The patient says their skin reddens painfully with sun exposure · a female patient 55 years old · by self-report, immunosuppression and a prior organ transplant · a moderate number of moles by the patient's own estimate · a dermoscopy image of a skin lesion — 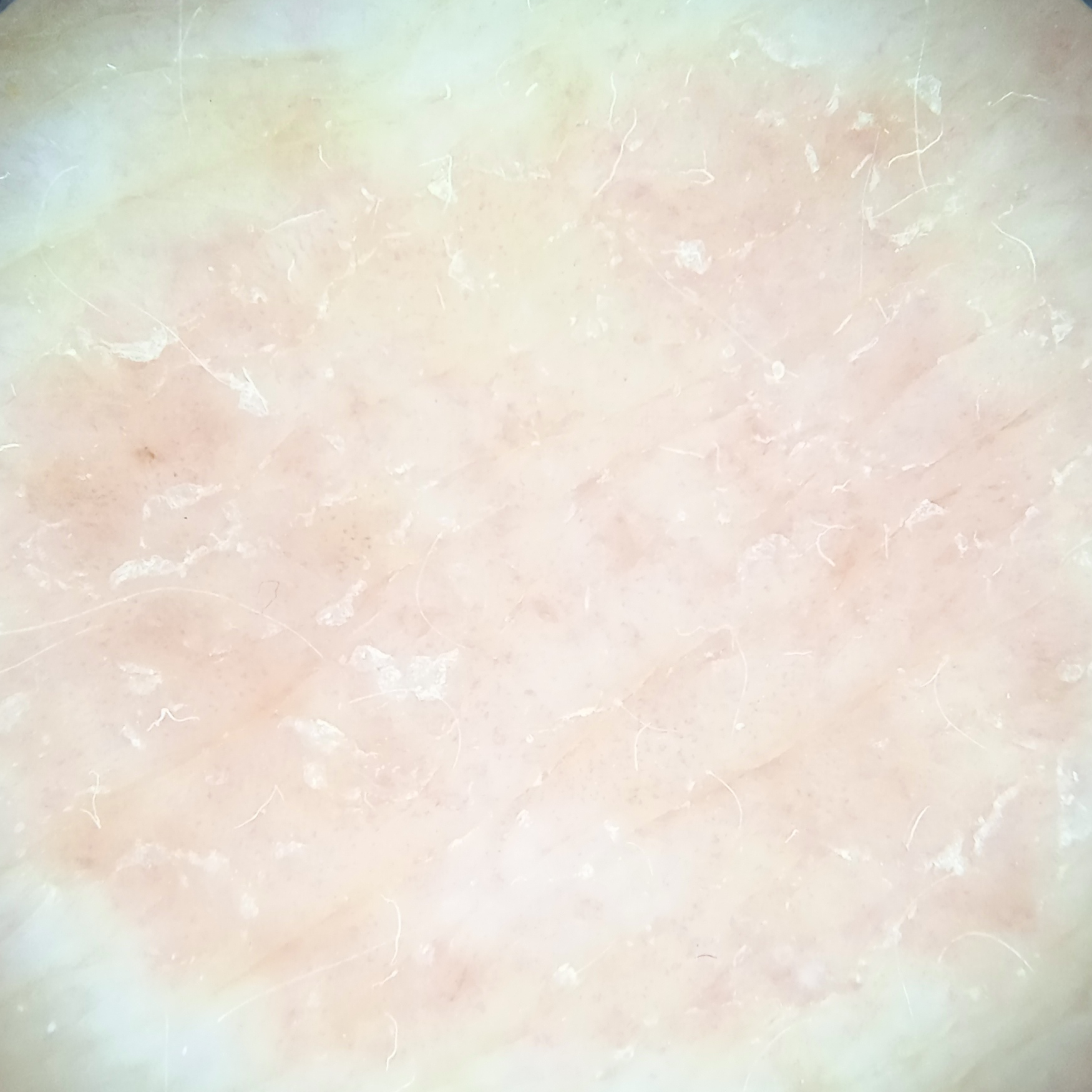{"lesion_size": {"diameter_mm": 13.2}, "diagnosis": {"name": "basal cell carcinoma", "malignancy": "malignant"}}